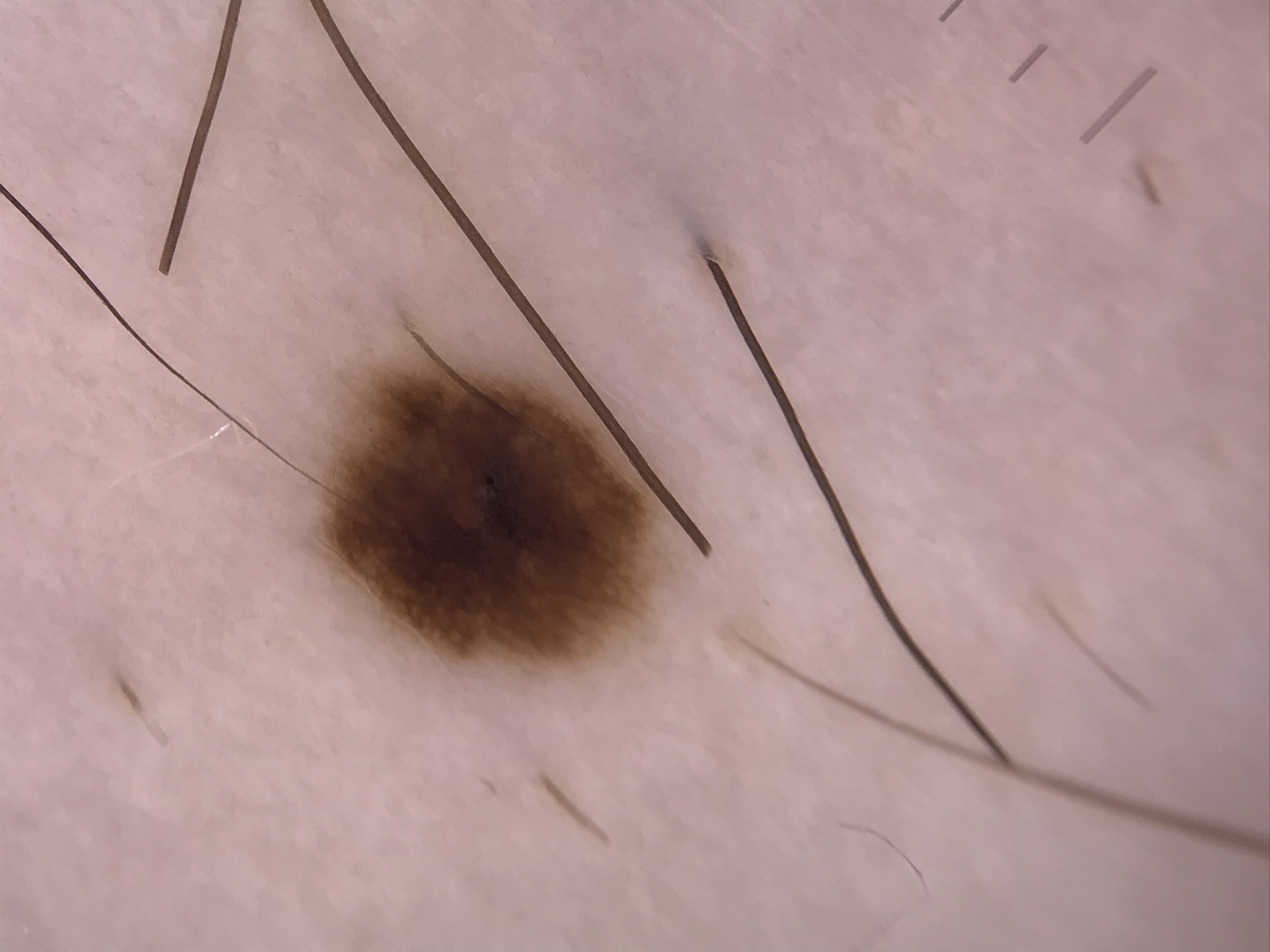image type — dermoscopy
diagnostic label — dysplastic junctional nevus (expert consensus)